A dermoscopy image of a skin lesion. A male patient age 78. Acquired for a research image collection, with no referral diagnosis — 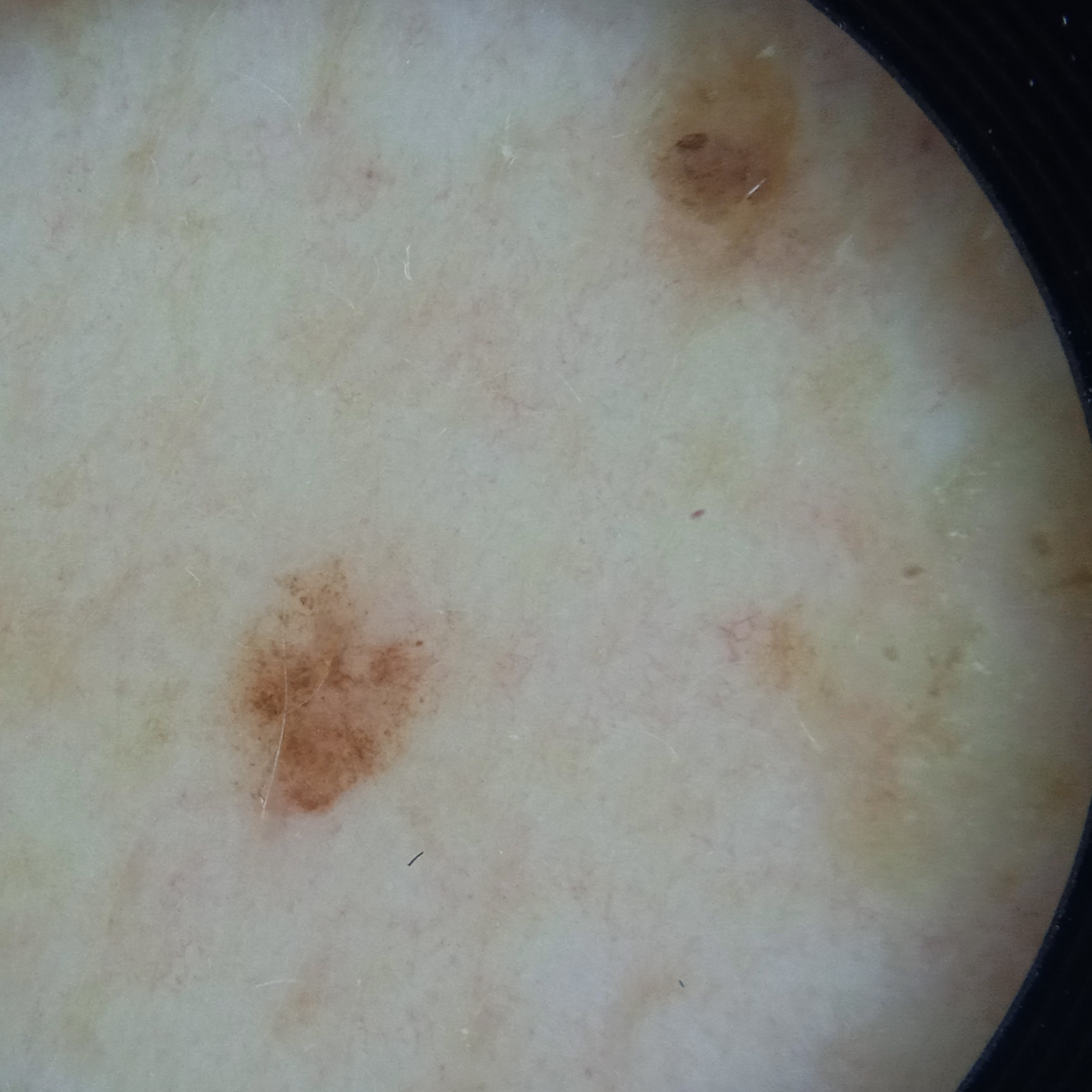lesion_location: the back
lesion_size:
  diameter_mm: 3.1
diagnosis:
  name: seborrheic keratosis
  malignancy: benign